A dermoscopy image of a single skin lesion.
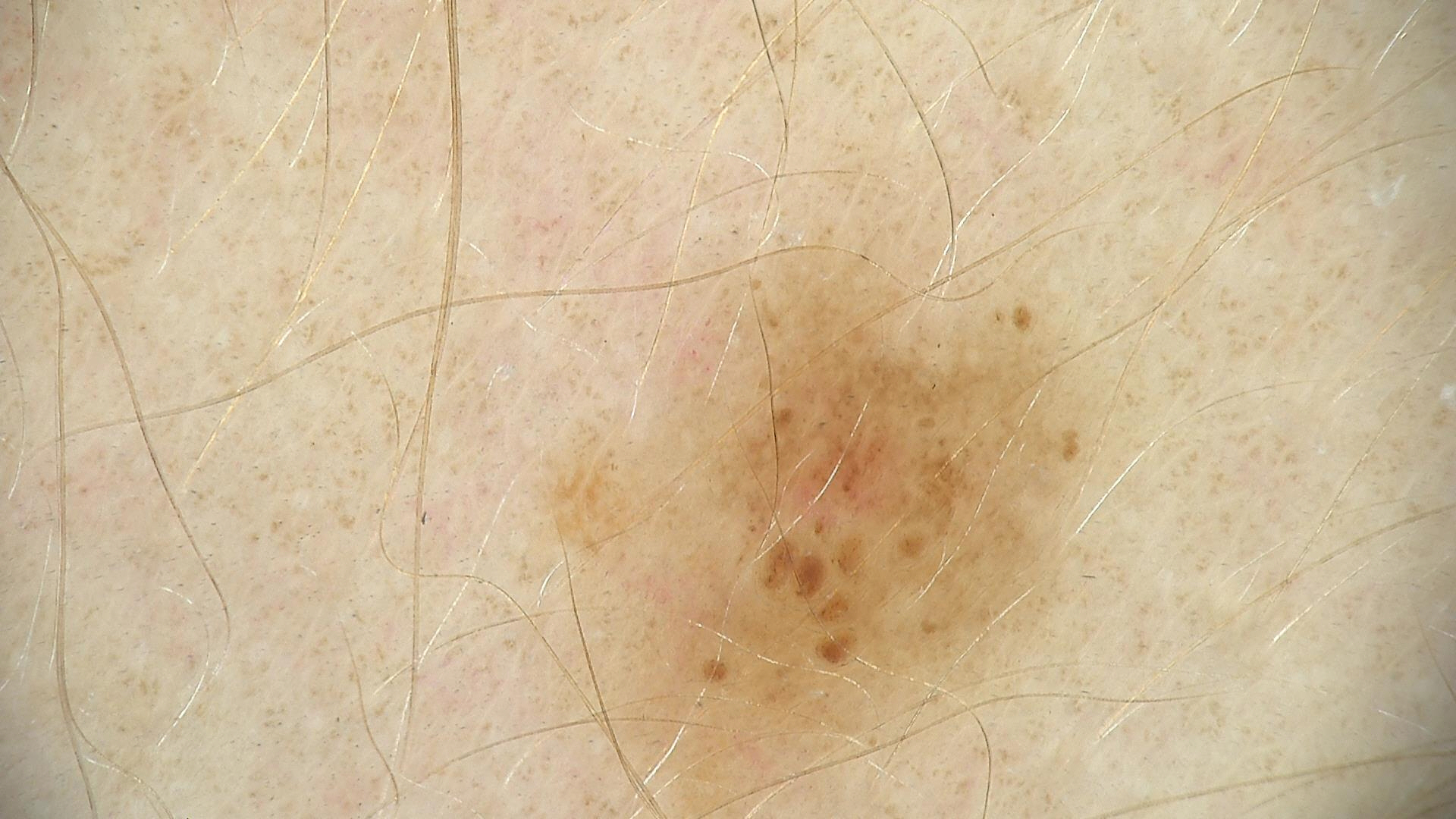assessment: dysplastic junctional nevus (expert consensus).